A dermoscopy image of a single skin lesion: 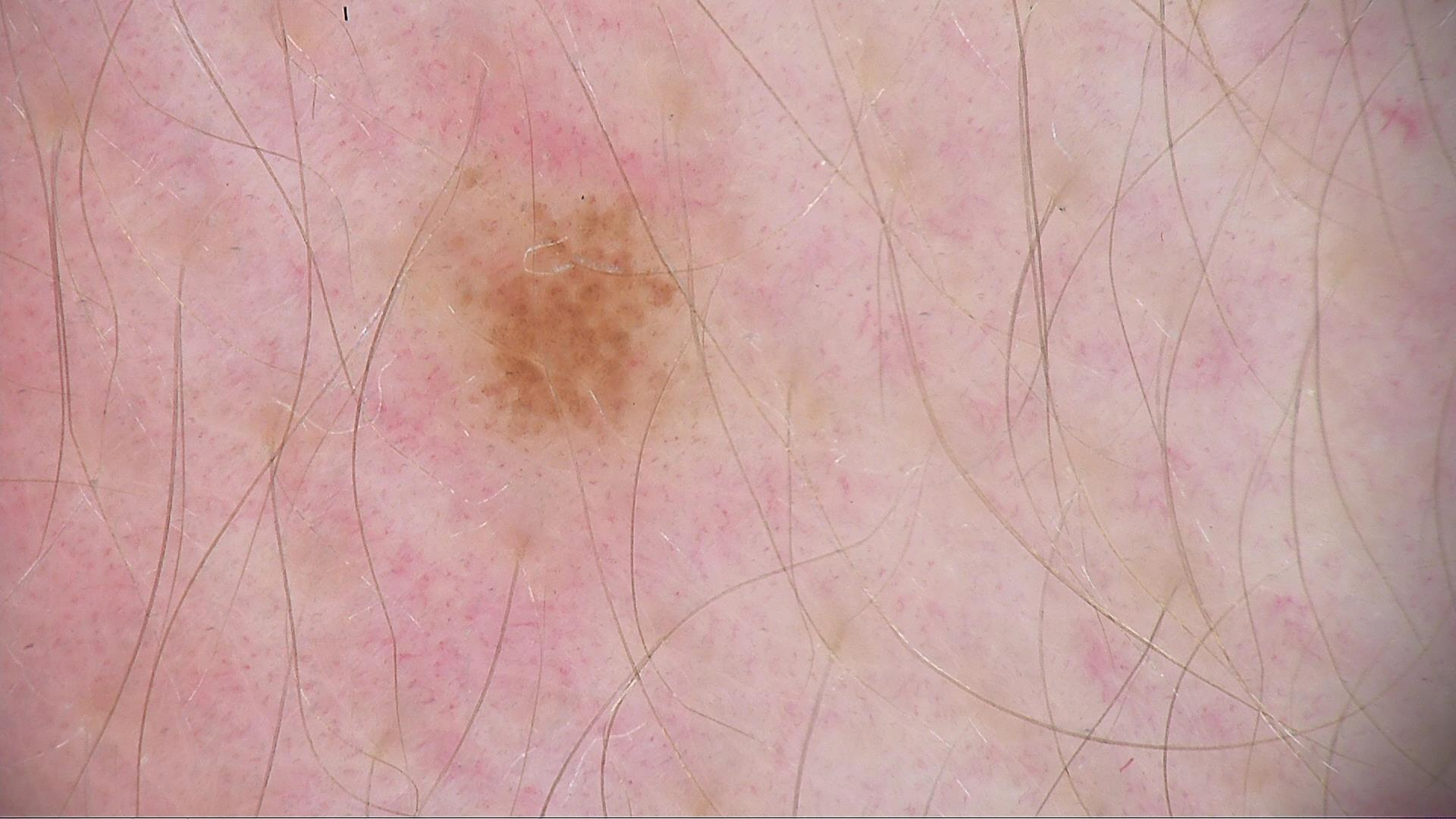Case:
- assessment — dysplastic junctional nevus (expert consensus)